A female subject, aged around 45 · a dermatoscopic image of a skin lesion:
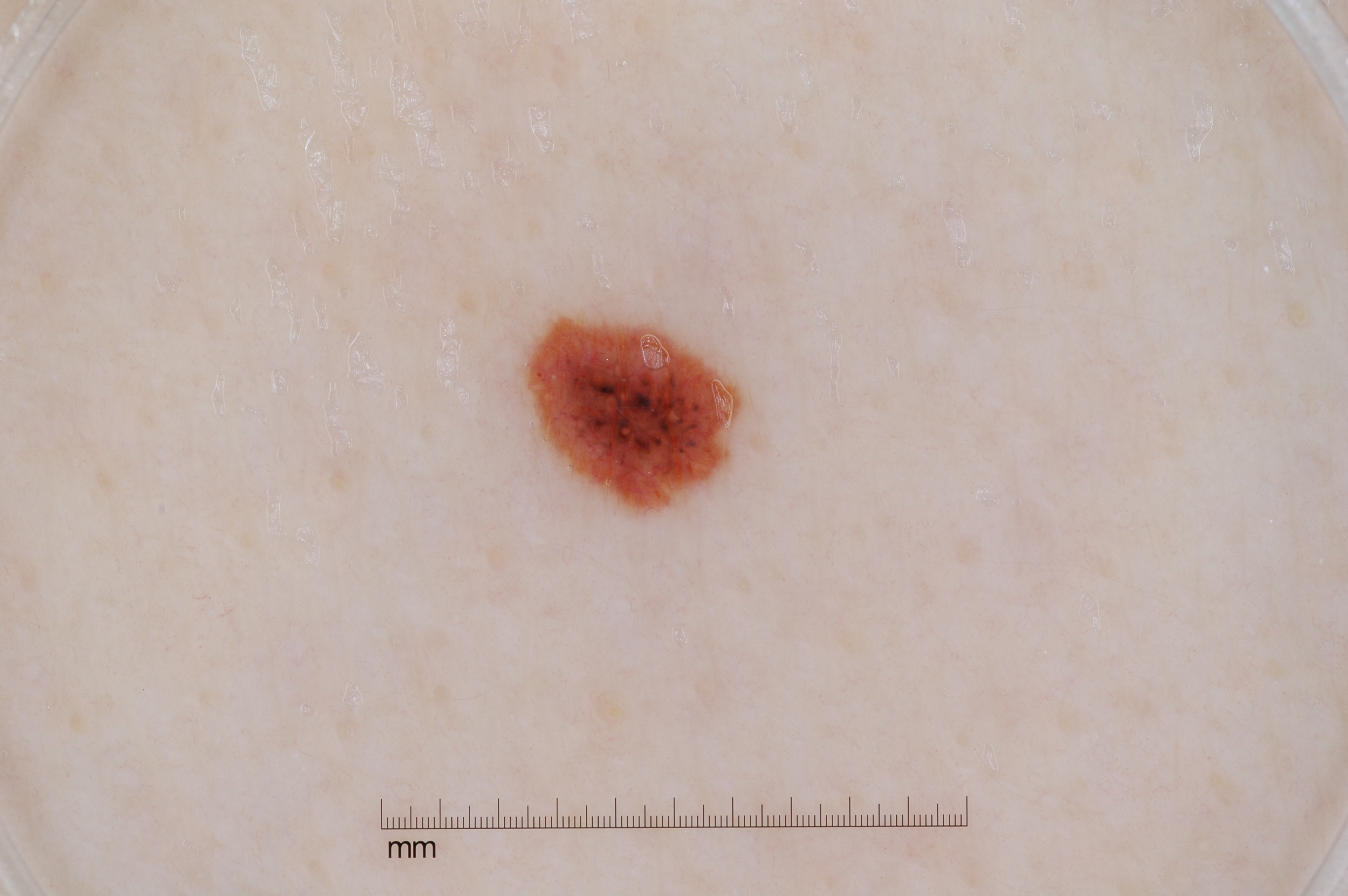As (left, top, right, bottom), the lesion is located at 527/315/747/511.
A small lesion occupying a minor part of the field.
Dermoscopically, the lesion shows no milia-like cysts, pigment network, streaks, or negative network.
The diagnostic assessment was a melanocytic nevus, a benign lesion.